A dermoscopic photograph of a skin lesion.
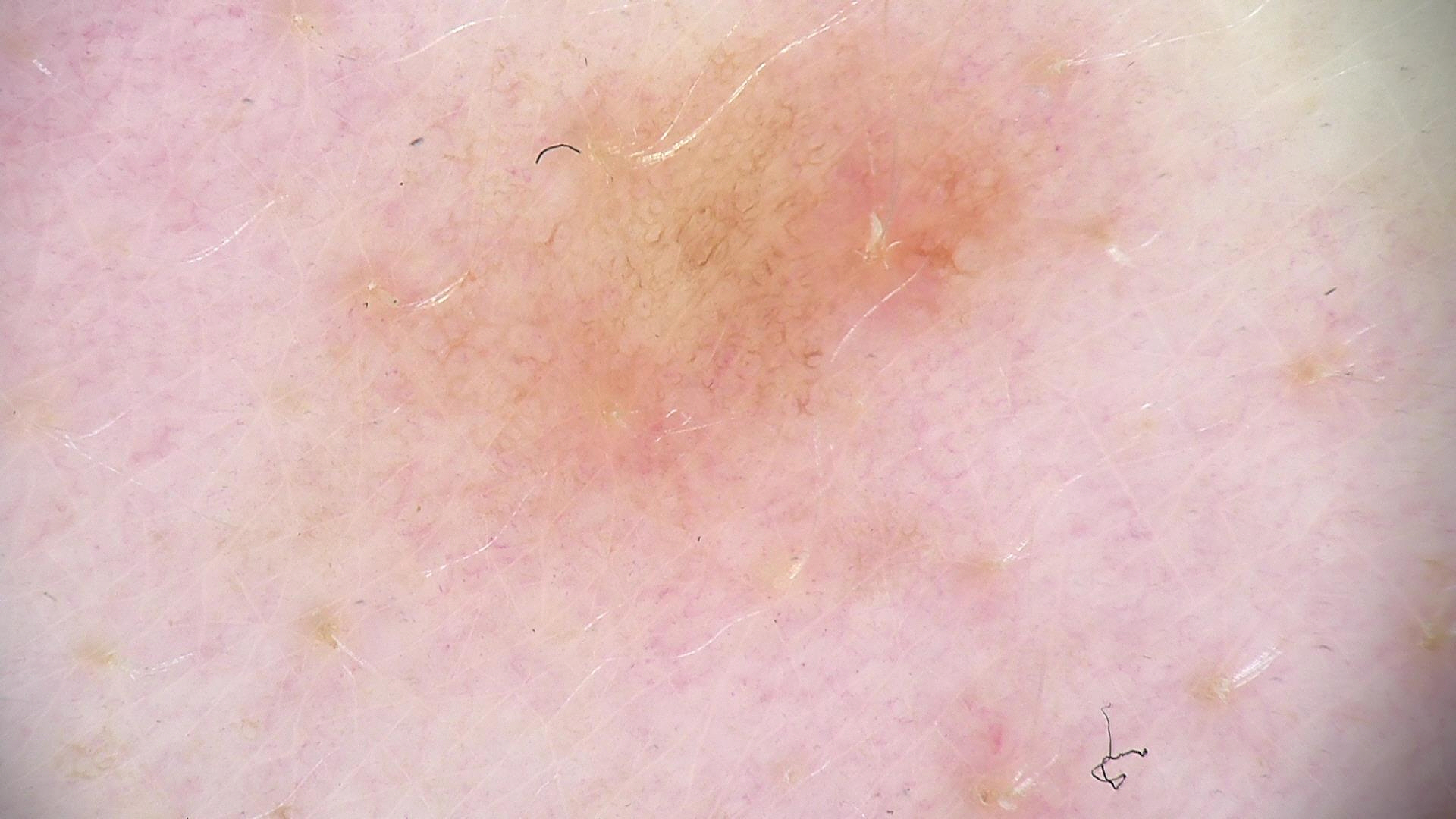Impression:
Diagnosed as a benign lesion — a dysplastic junctional nevus.